Close-up view — 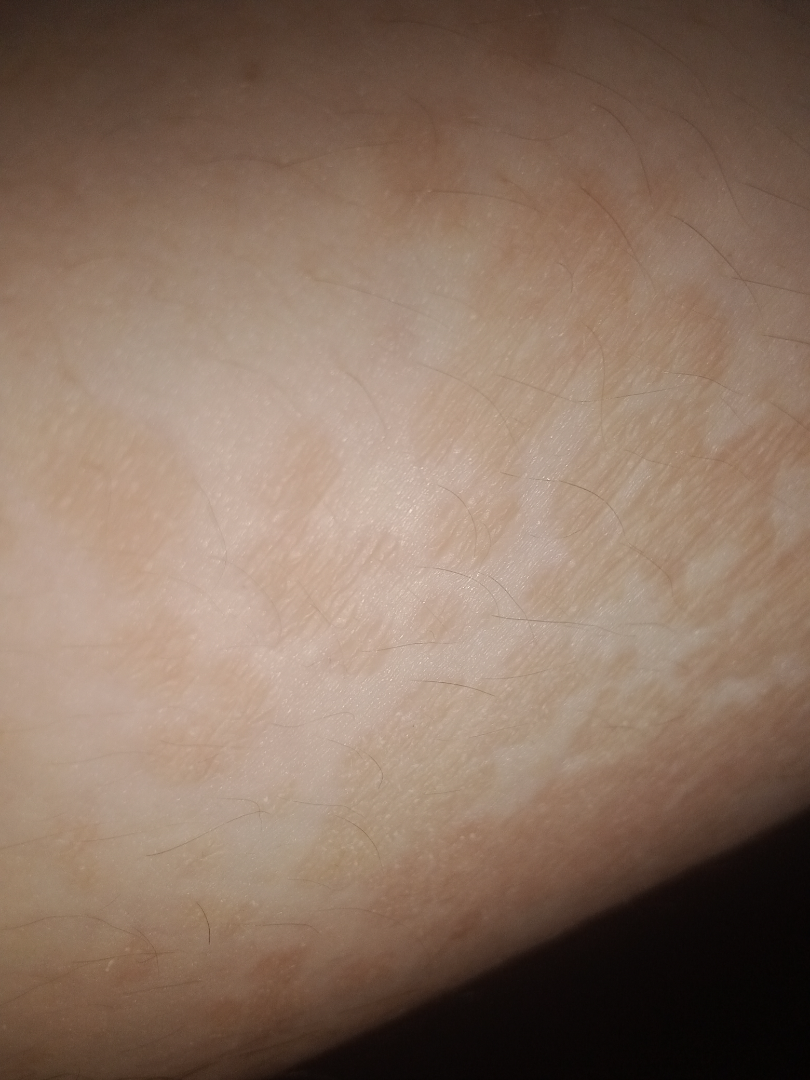– dermatologist impression: most likely Tinea Versicolor; possibly Tinea; also on the differential is Eczema